Female patient, age 50–59; an image taken at a distance; located on the leg — 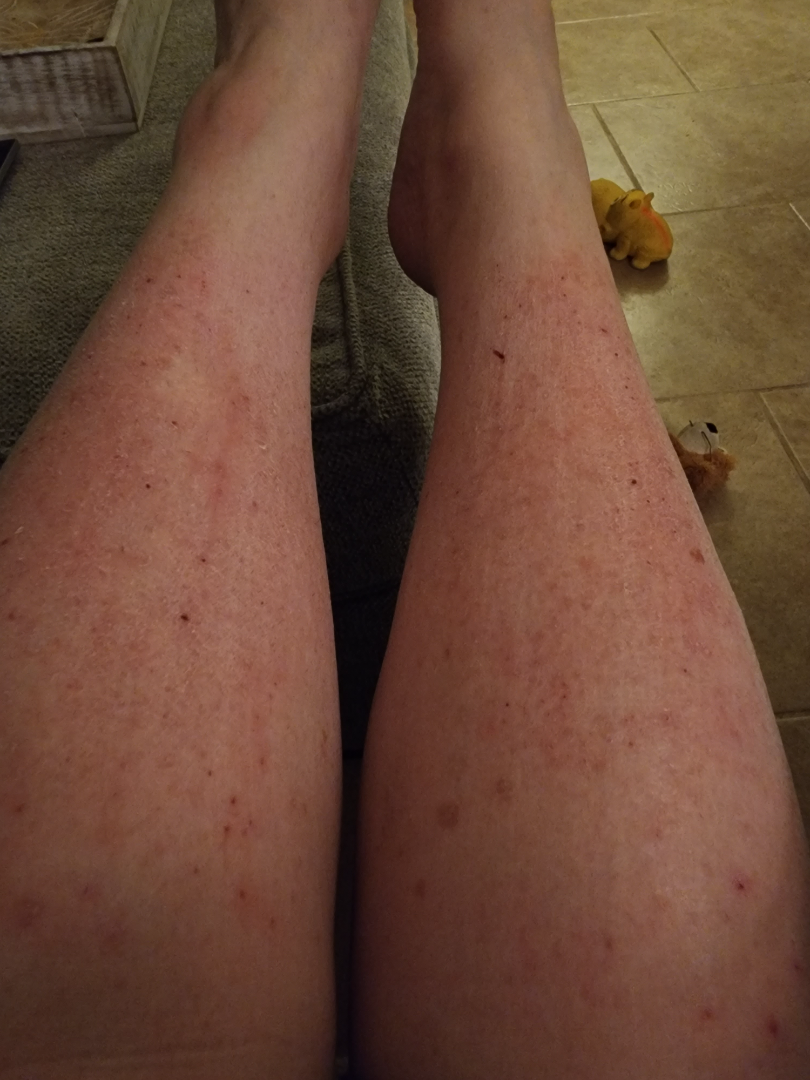<case>
<differential>Eczema</differential>
</case>